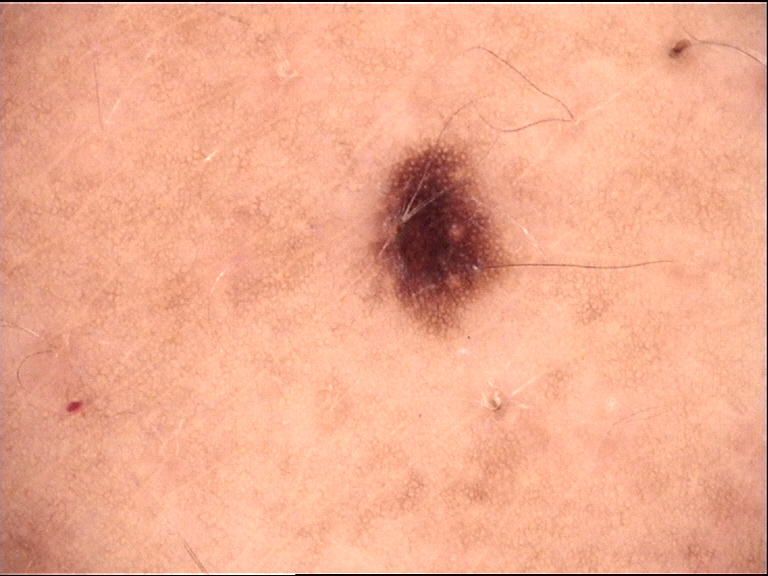Impression:
Labeled as a dysplastic junctional nevus.